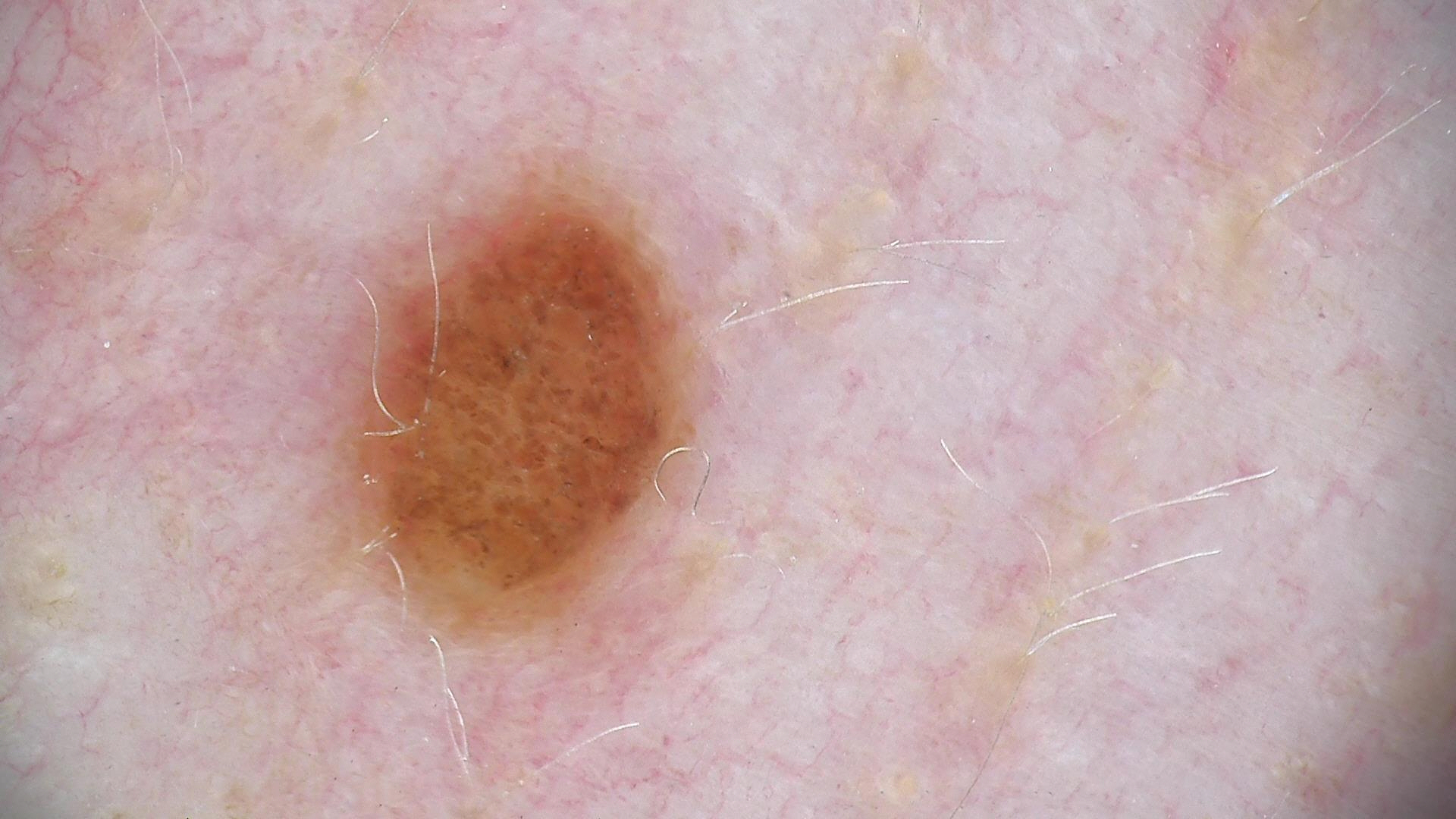– modality · dermatoscopy
– classification · banal
– class · compound nevus (expert consensus)